The patient is 30–39, female; the condition has been present for about one day; the lesion is associated with bothersome appearance; located on the arm; self-categorized by the patient as a rash; close-up view.
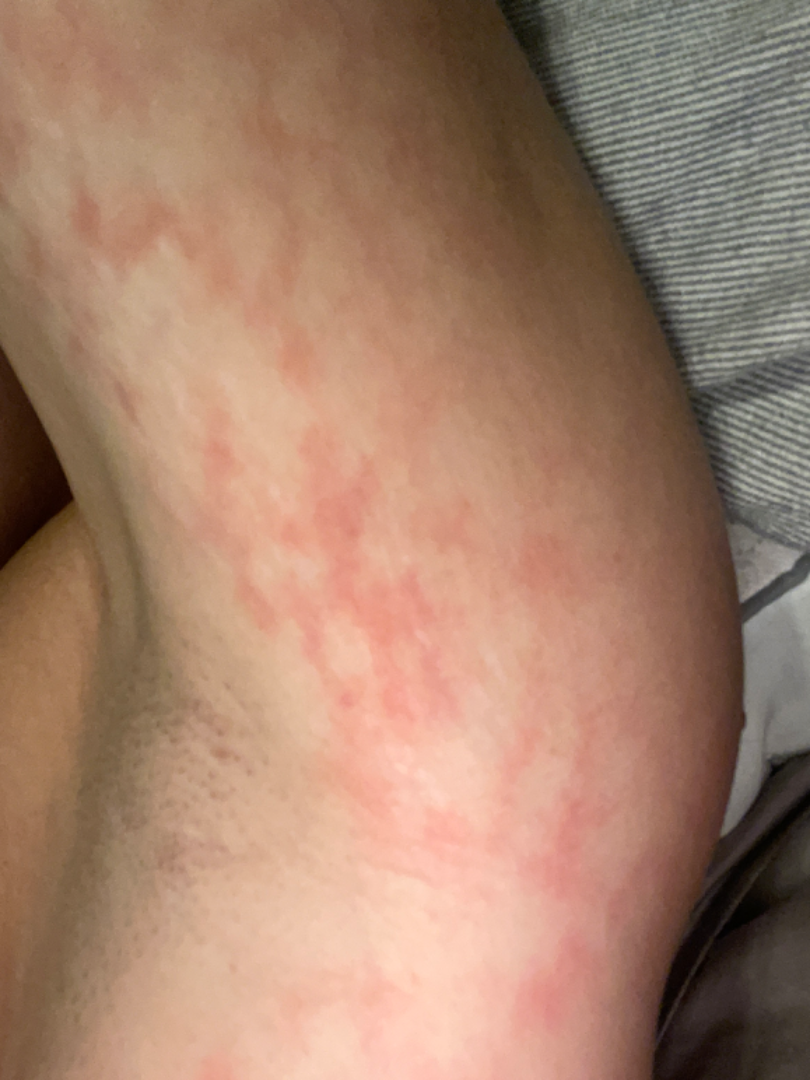Erythema ab igne, Livedoid vasculopathy and Erythema gyratum repens were considered with similar weight.